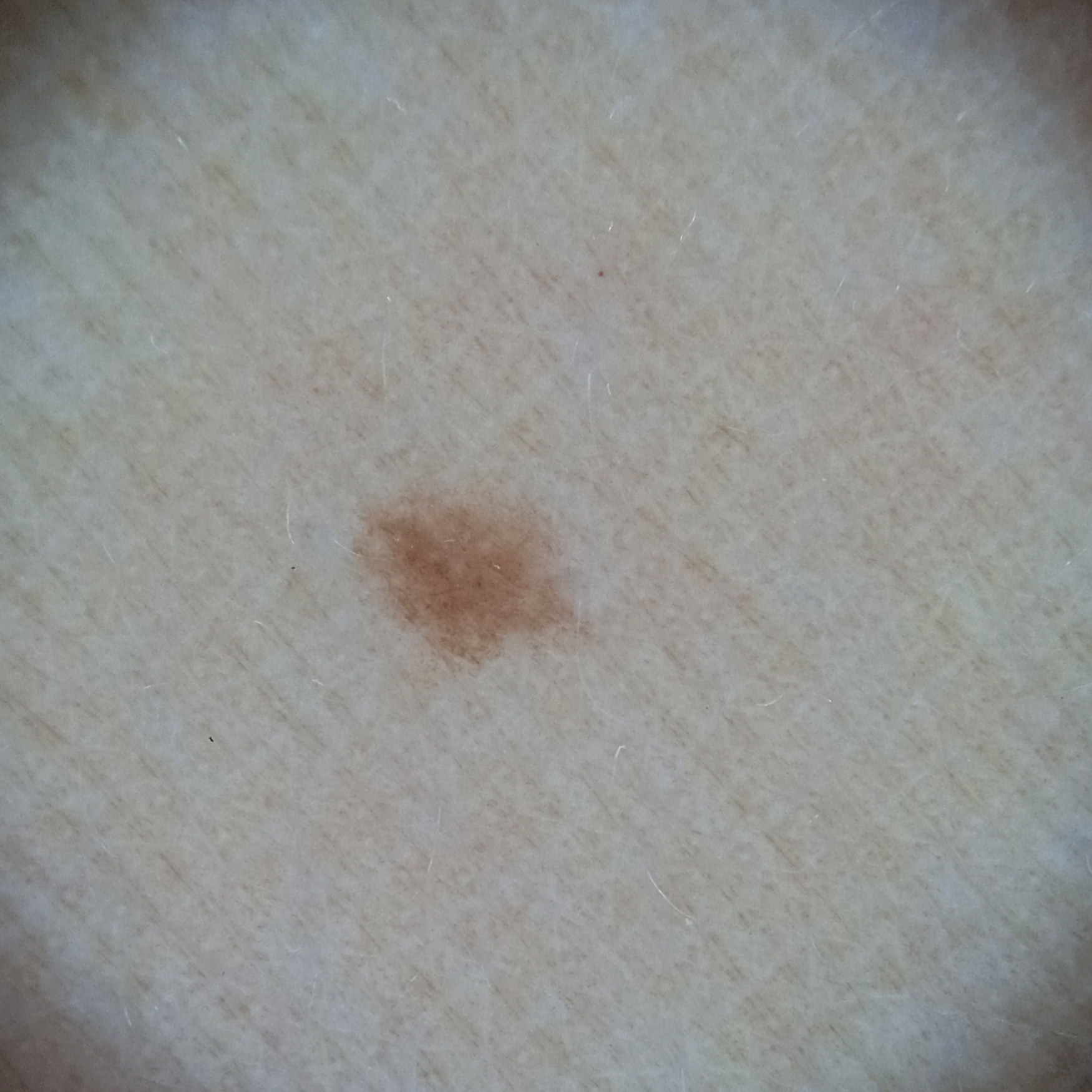* risk factors · a history of sunbed use
* sun reaction · skin tans without first burning
* nevus count · a moderate number of melanocytic nevi
* assessment · melanocytic nevus (dermatologist consensus)